A skin lesion imaged with a dermatoscope.
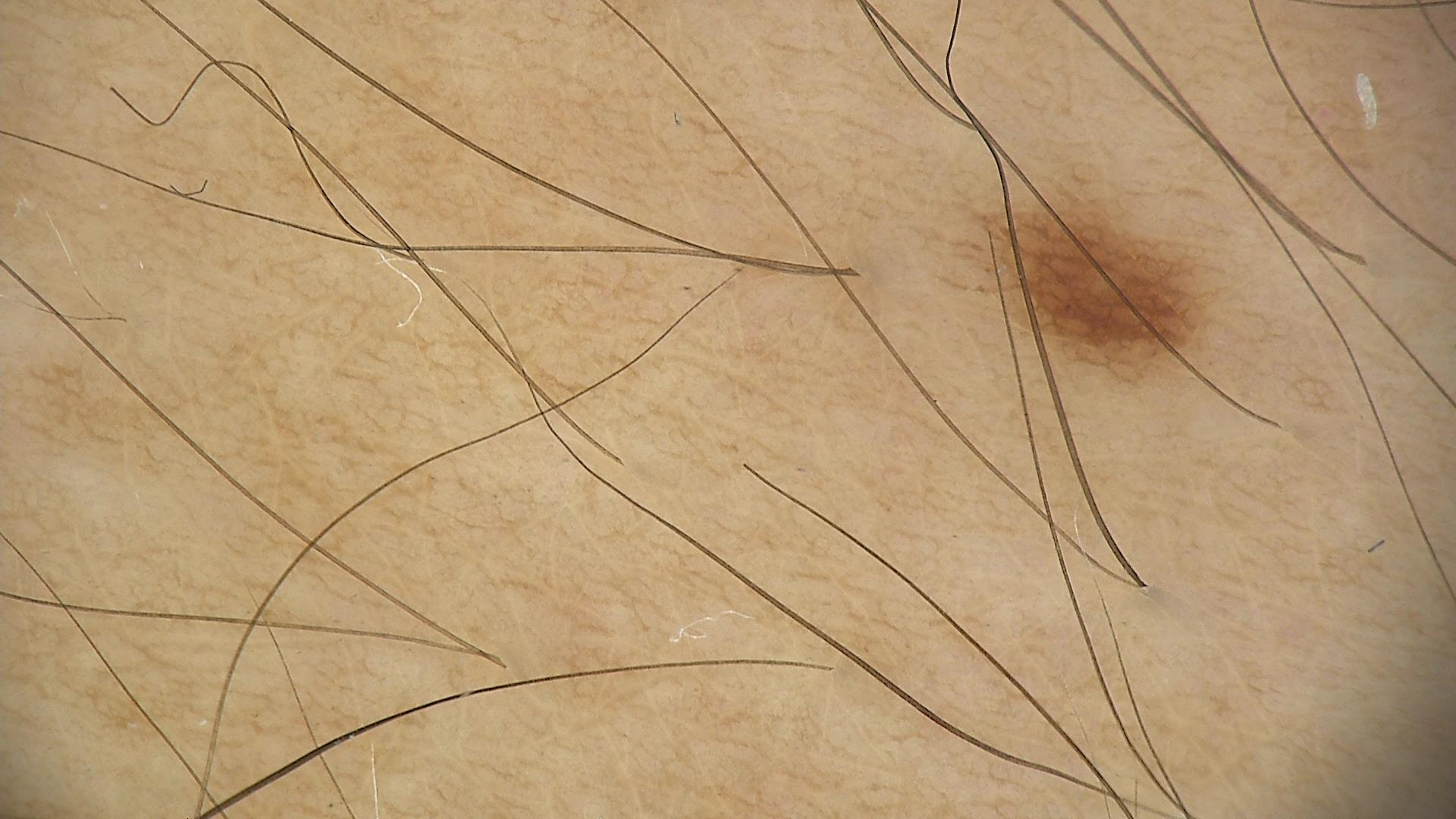The diagnosis was a benign lesion — a dysplastic junctional nevus.